A dermoscopic close-up of a skin lesion: 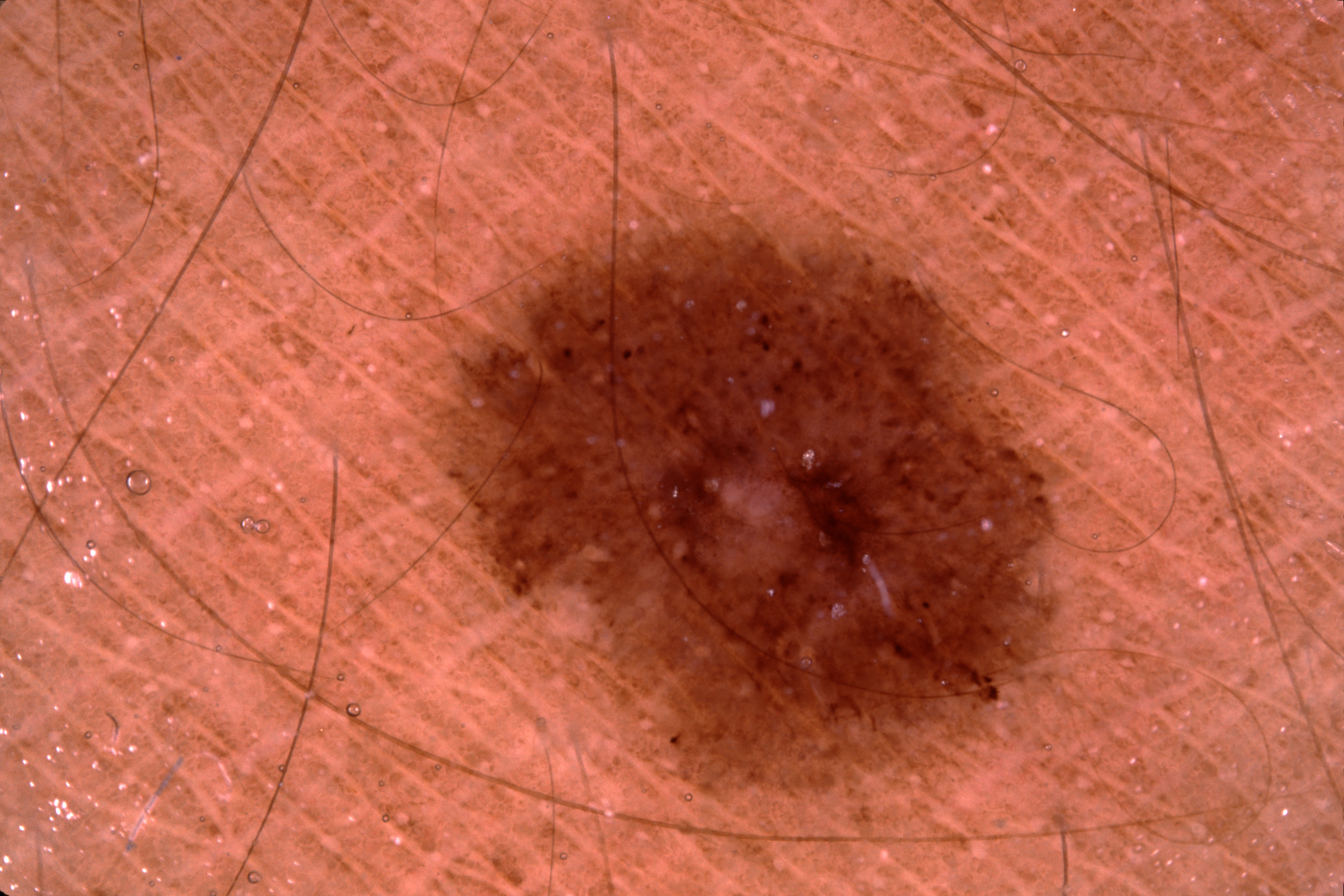In (x1, y1, x2, y2) order, the lesion is bounded by bbox(441, 214, 1067, 797).
Clinically diagnosed as a melanocytic nevus.